A female subject aged 48; collected as part of a research study, without a referral diagnosis; a dermatoscopic image of a skin lesion: 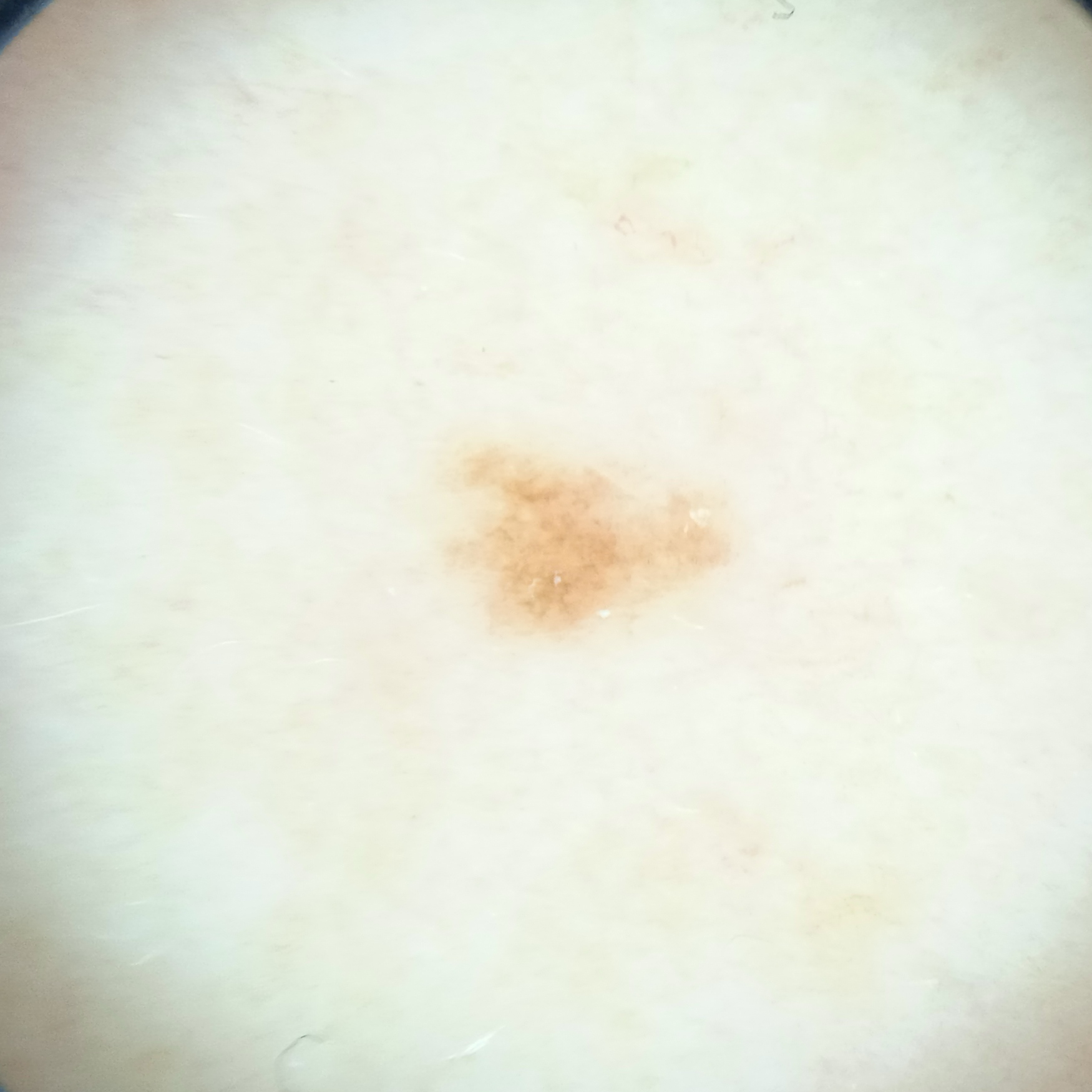The lesion involves the back. The lesion measures approximately 3.7 mm. The consensus diagnosis for this lesion was a melanocytic nevus.